The patient is a female aged approximately 25; dermoscopy of a skin lesion.
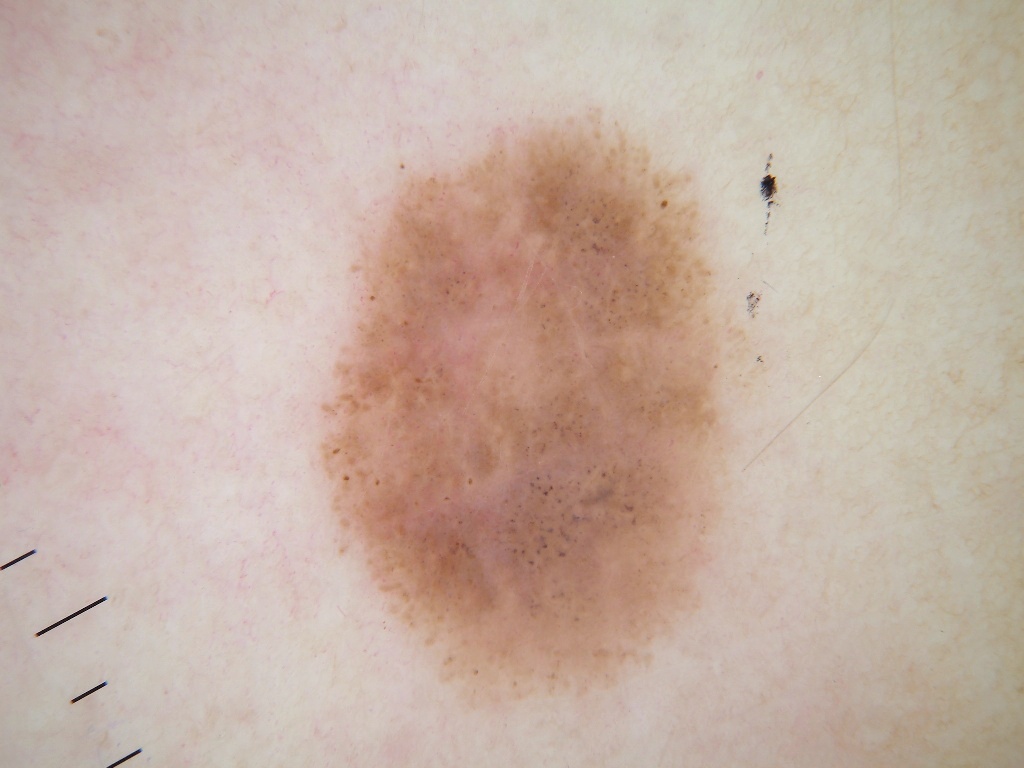{
  "lesion_location": {
    "bbox_xyxy": [
      319,
      113,
      739,
      736
    ]
  },
  "dermoscopic_features": {
    "present": [
      "globules",
      "streaks",
      "negative network"
    ],
    "absent": [
      "pigment network",
      "milia-like cysts"
    ]
  },
  "diagnosis": {
    "name": "melanocytic nevus",
    "malignancy": "benign",
    "lineage": "melanocytic",
    "provenance": "clinical"
  }
}